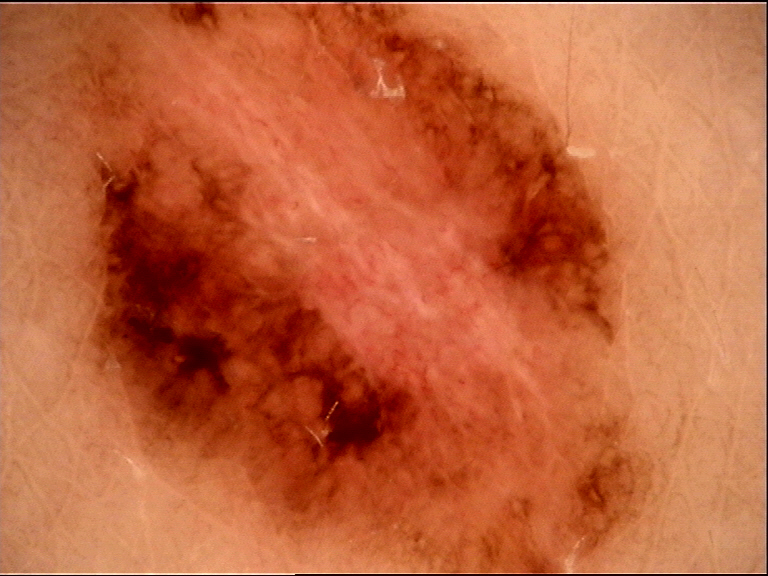Summary:
A dermoscopy image of a single skin lesion.
Conclusion:
Histopathology confirmed a malignancy — a melanoma.